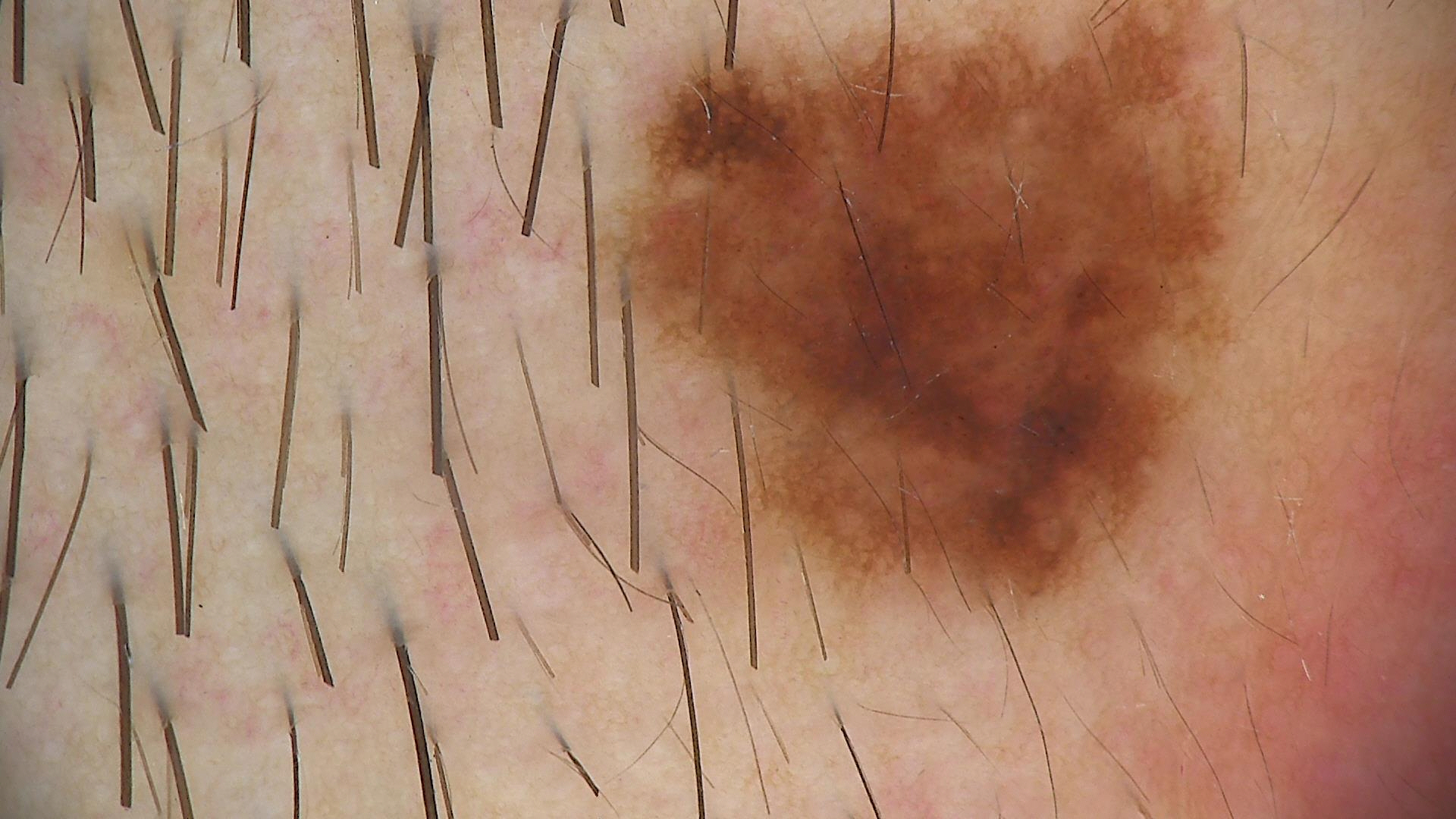Summary:
A dermatoscopic image of a skin lesion.
Diagnosis:
Confirmed on histopathology as a malignancy — a melanoma.